The photograph is a close-up of the affected area, the lesion involves the front of the torso:
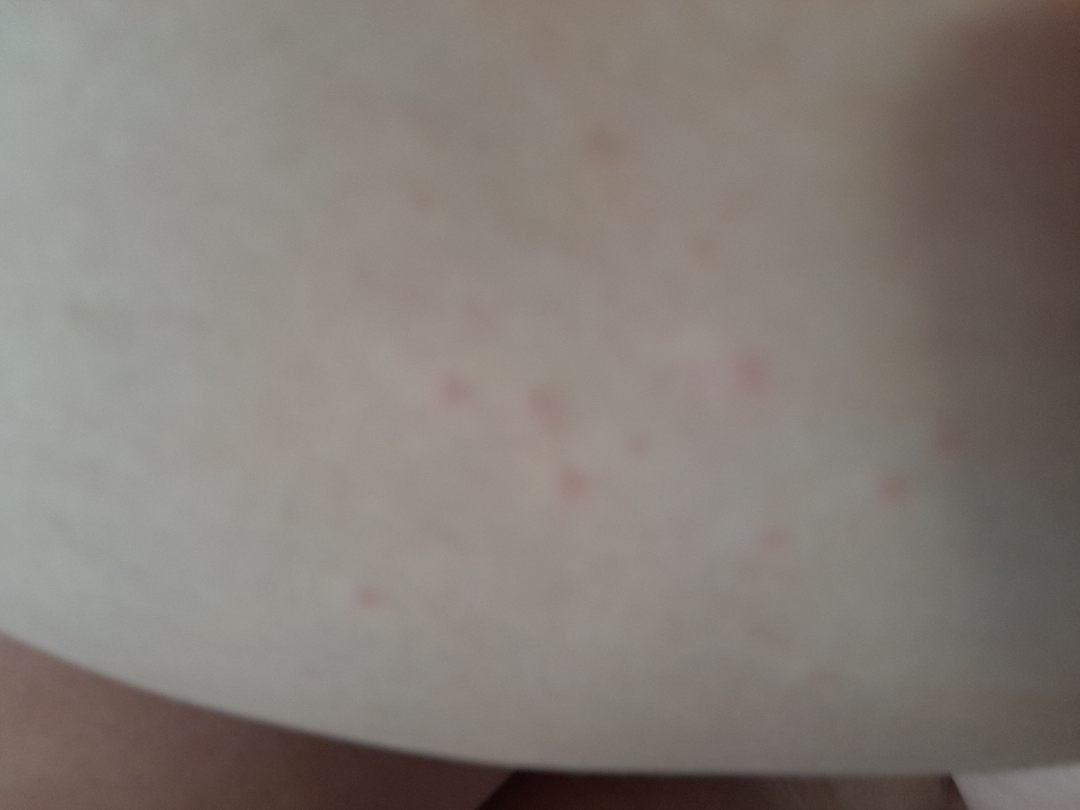Diagnostic features were not clearly distinguishable in this photograph.
Skin tone: FST III.
The contributor reports the lesion is raised or bumpy.
The patient described the issue as skin that appeared healthy to them.
Present for about one day.
The patient reported no relevant symptoms from the lesion.